The patient describes having a moderate number of moles · collected as part of a research study, without a referral diagnosis:
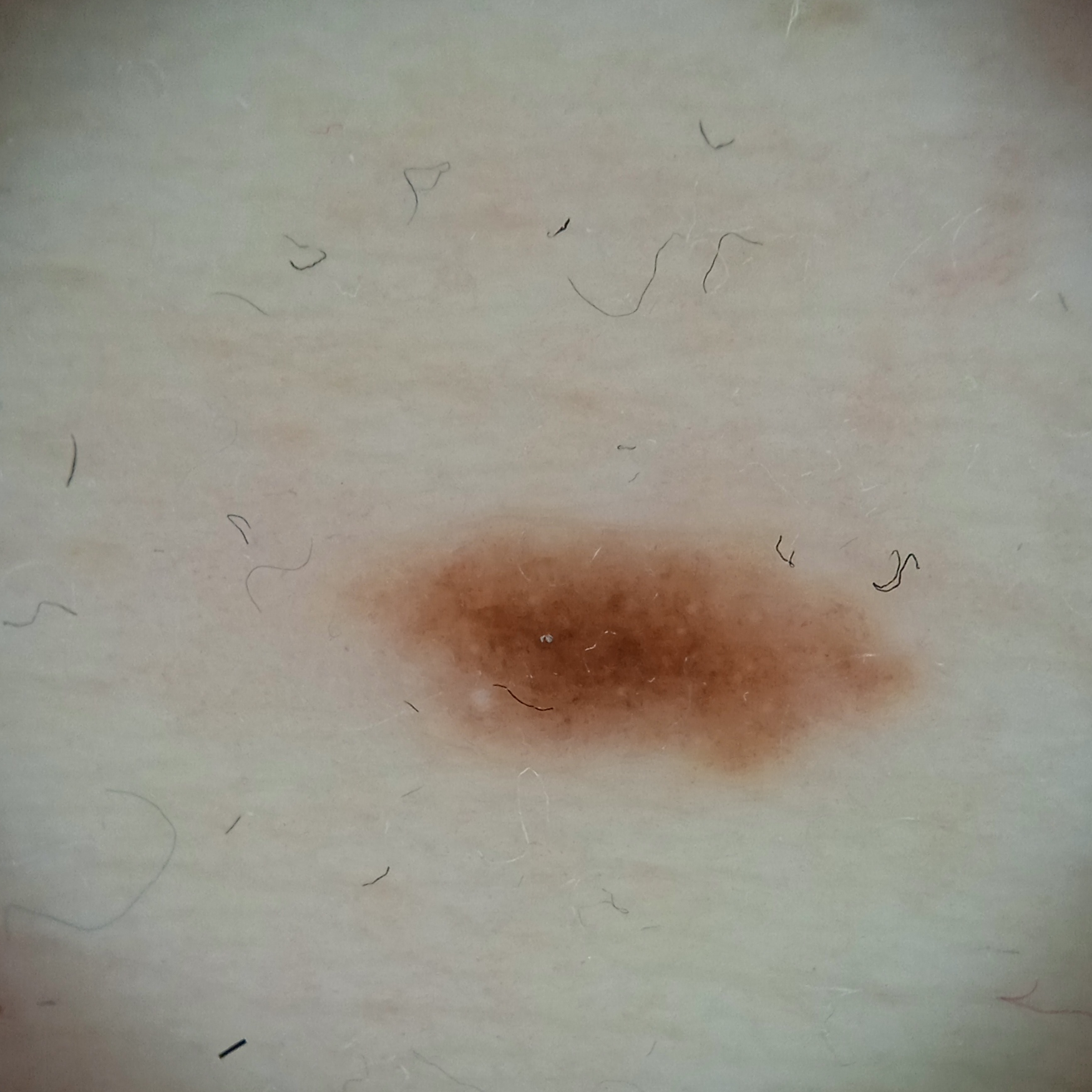Located on the torso. Measuring roughly 6.3 mm. The lesion was assessed as a melanocytic nevus.